A skin lesion imaged with a dermatoscope.
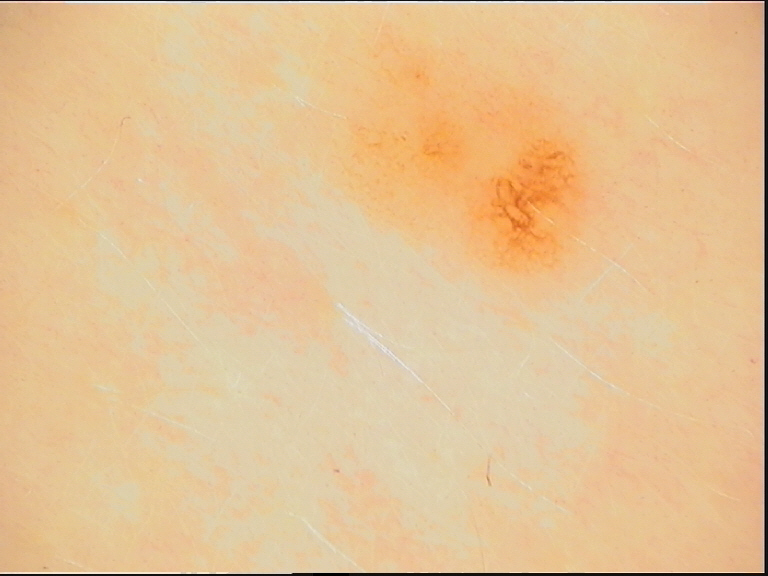Diagnosed as a dysplastic junctional nevus.